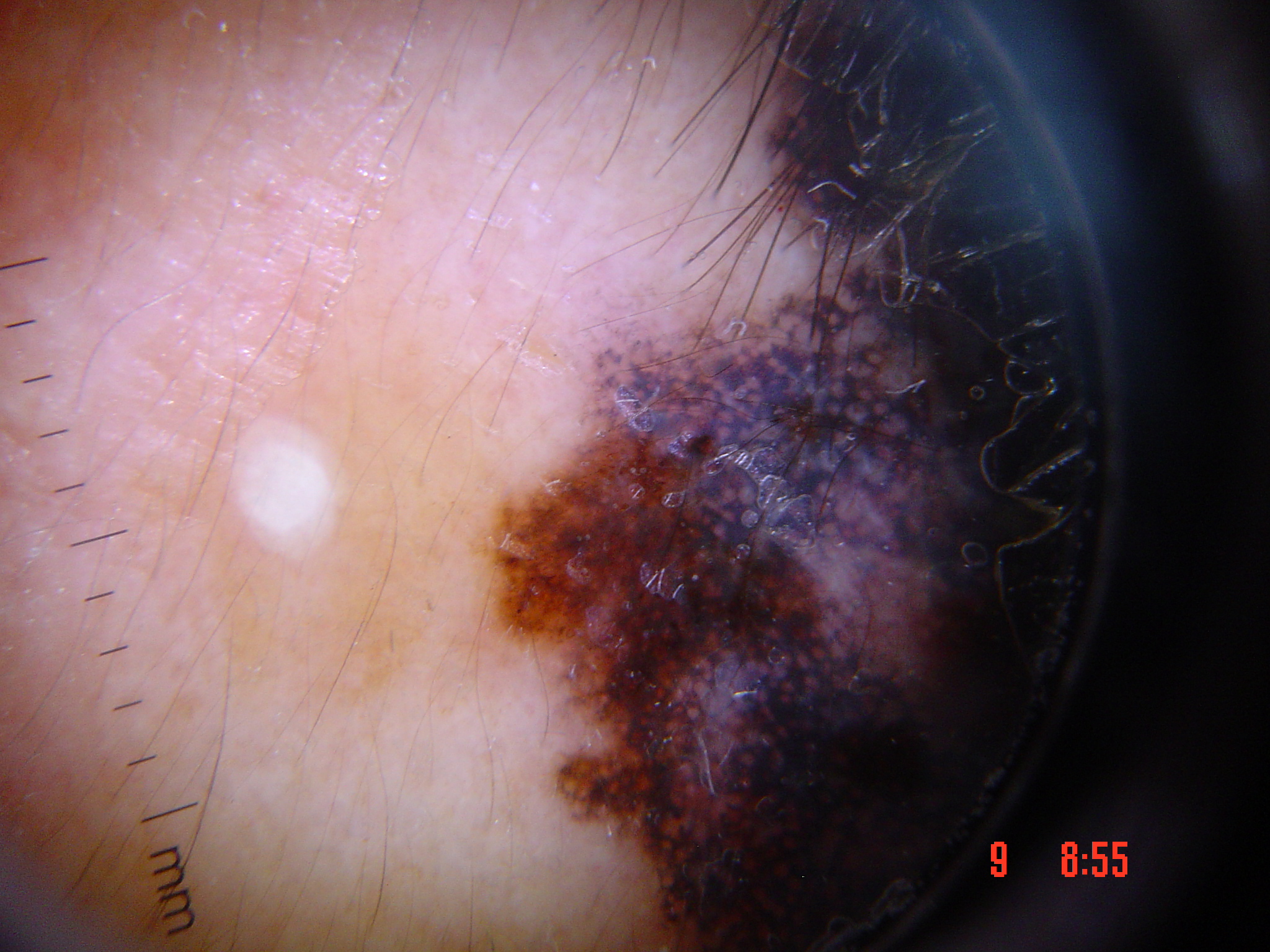Q: What kind of image is this?
A: dermatoscopy
Q: What is this lesion?
A: lentigo maligna (biopsy-proven)